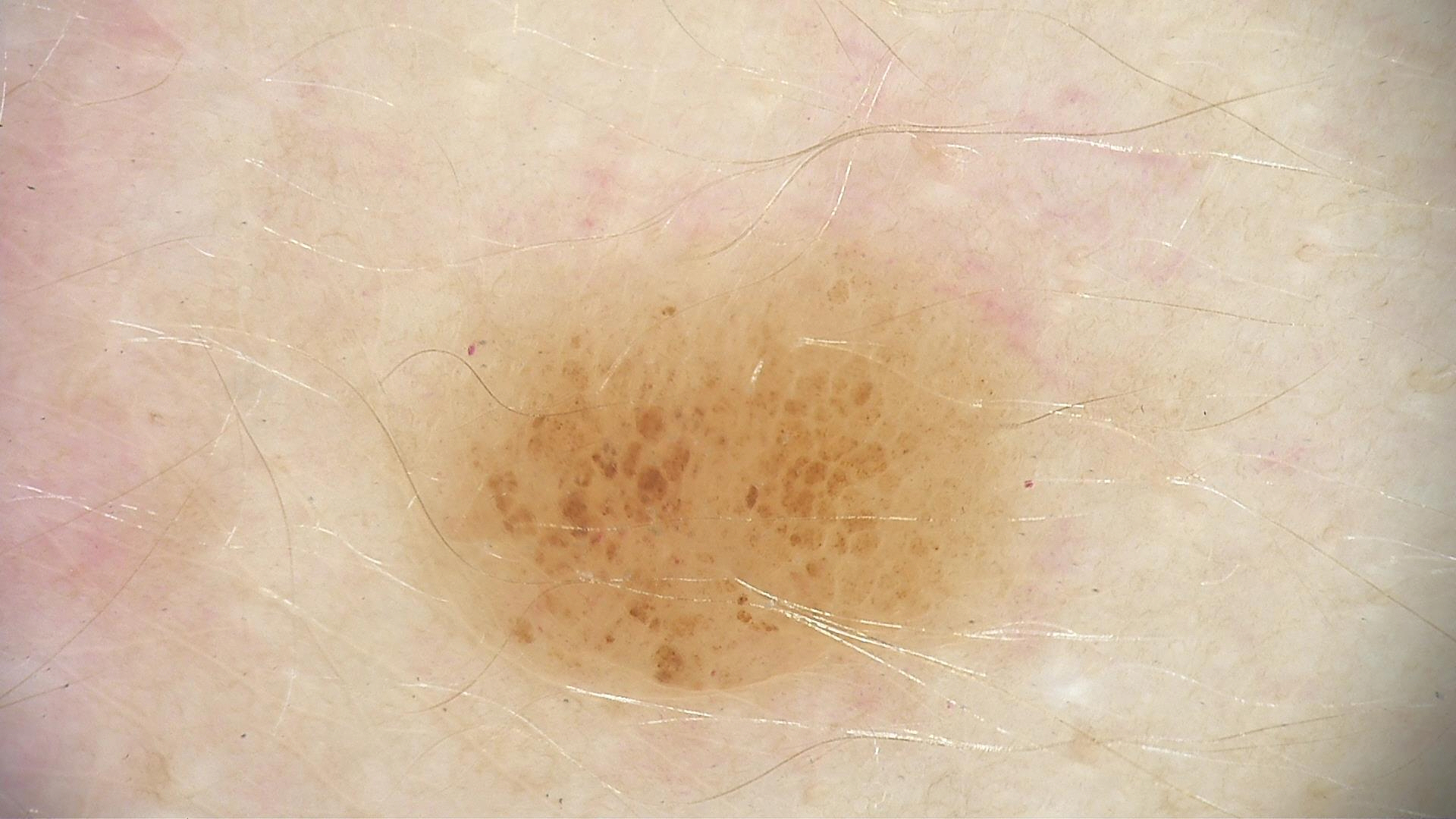The diagnosis was a compound nevus.